This is a close-up image, located on the arm and leg:
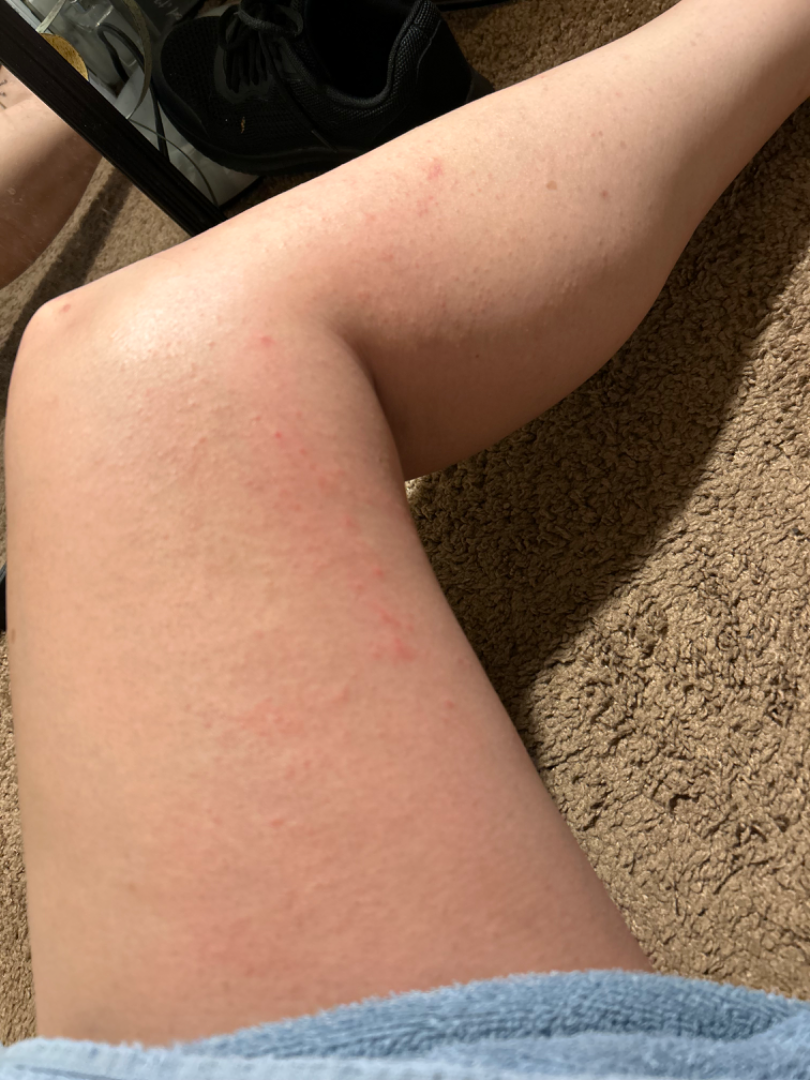Q: What was the assessment?
A: not assessable
Q: Reported symptoms?
A: itching
Q: Texture?
A: raised or bumpy
Q: How does the patient describe it?
A: skin that appeared healthy to them
Q: Constitutional symptoms?
A: none reported